A dermatoscopic image of a skin lesion:
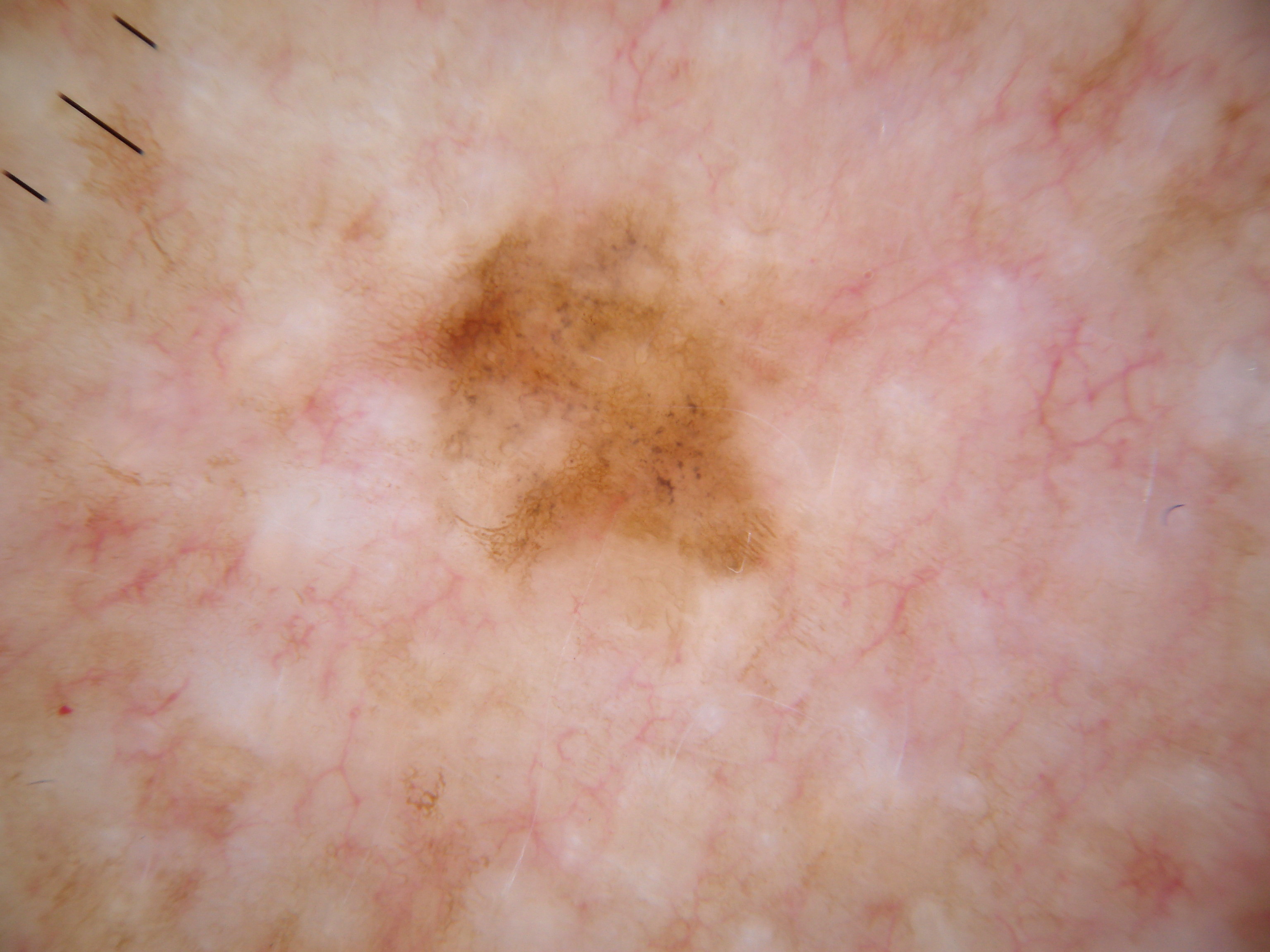{
  "dermoscopic_features": {
    "present": [
      "globules",
      "pigment network",
      "streaks"
    ],
    "absent": [
      "milia-like cysts",
      "negative network"
    ]
  },
  "lesion_location": {
    "bbox_xyxy": [
      369,
      184,
      878,
      628
    ]
  },
  "lesion_extent": {
    "approx_field_fraction_pct": 10
  },
  "diagnosis": {
    "name": "melanoma",
    "malignancy": "malignant",
    "lineage": "melanocytic",
    "provenance": "histopathology"
  }
}